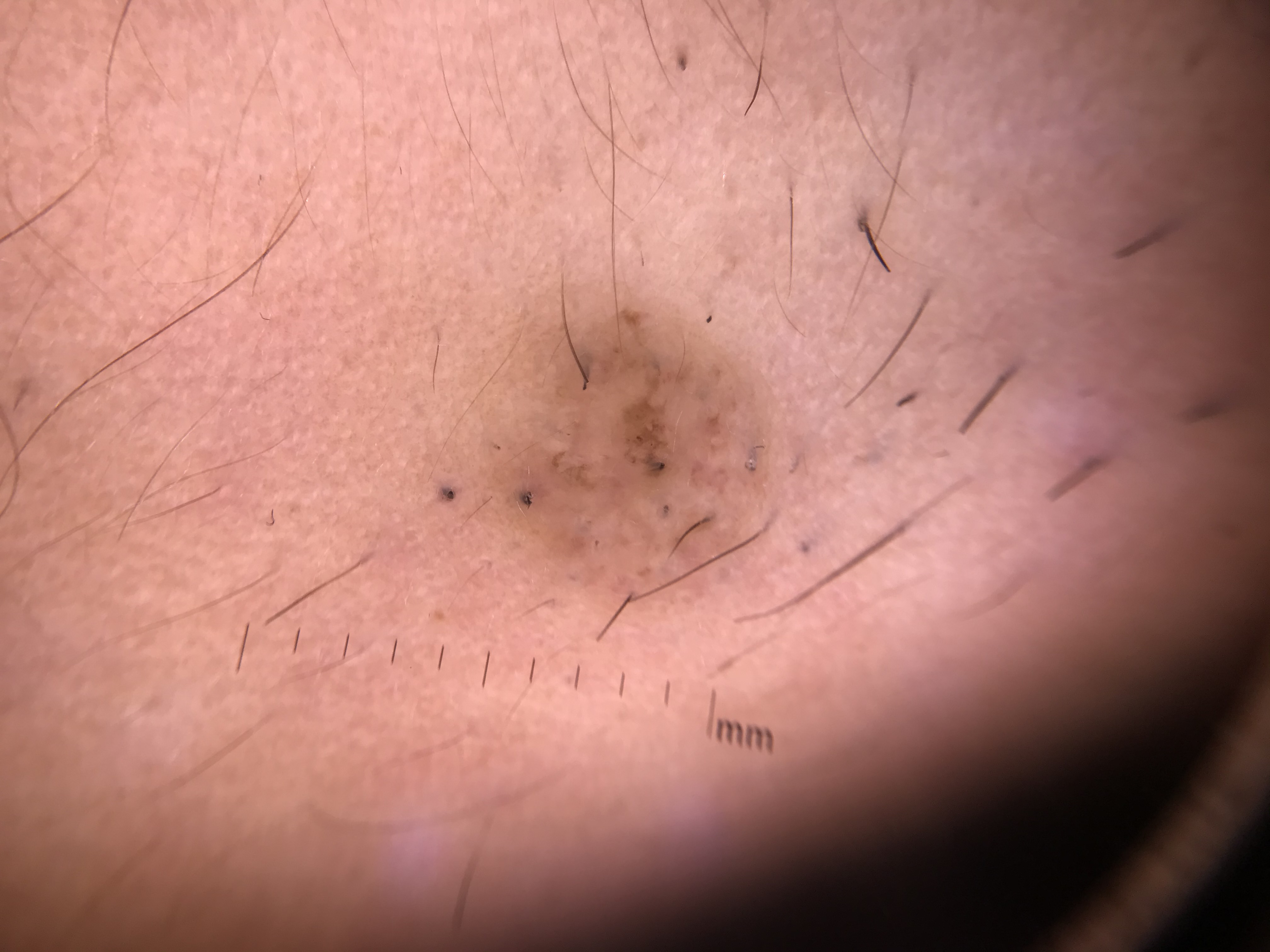Classified as a compound lesion — a Miescher nevus.